A close-up photograph, the lesion involves the arm, the subject is male.
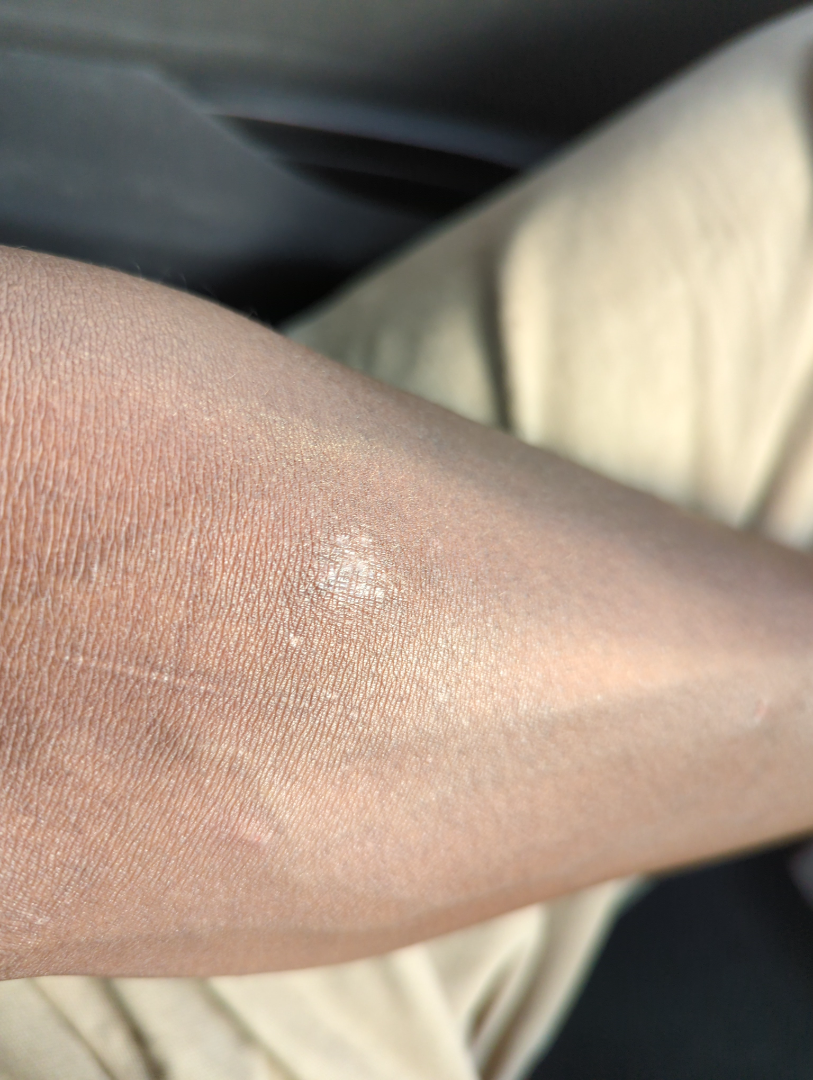Q: What conditions are considered?
A: reviewed remotely by one dermatologist: the differential is split between Cyst, Psoriasis and Lichen Simplex Chronicus